A contact-polarized dermoscopy image of a skin lesion. The chart records no first-degree relative with melanoma and no prior melanoma. A female subject about 20 years old — 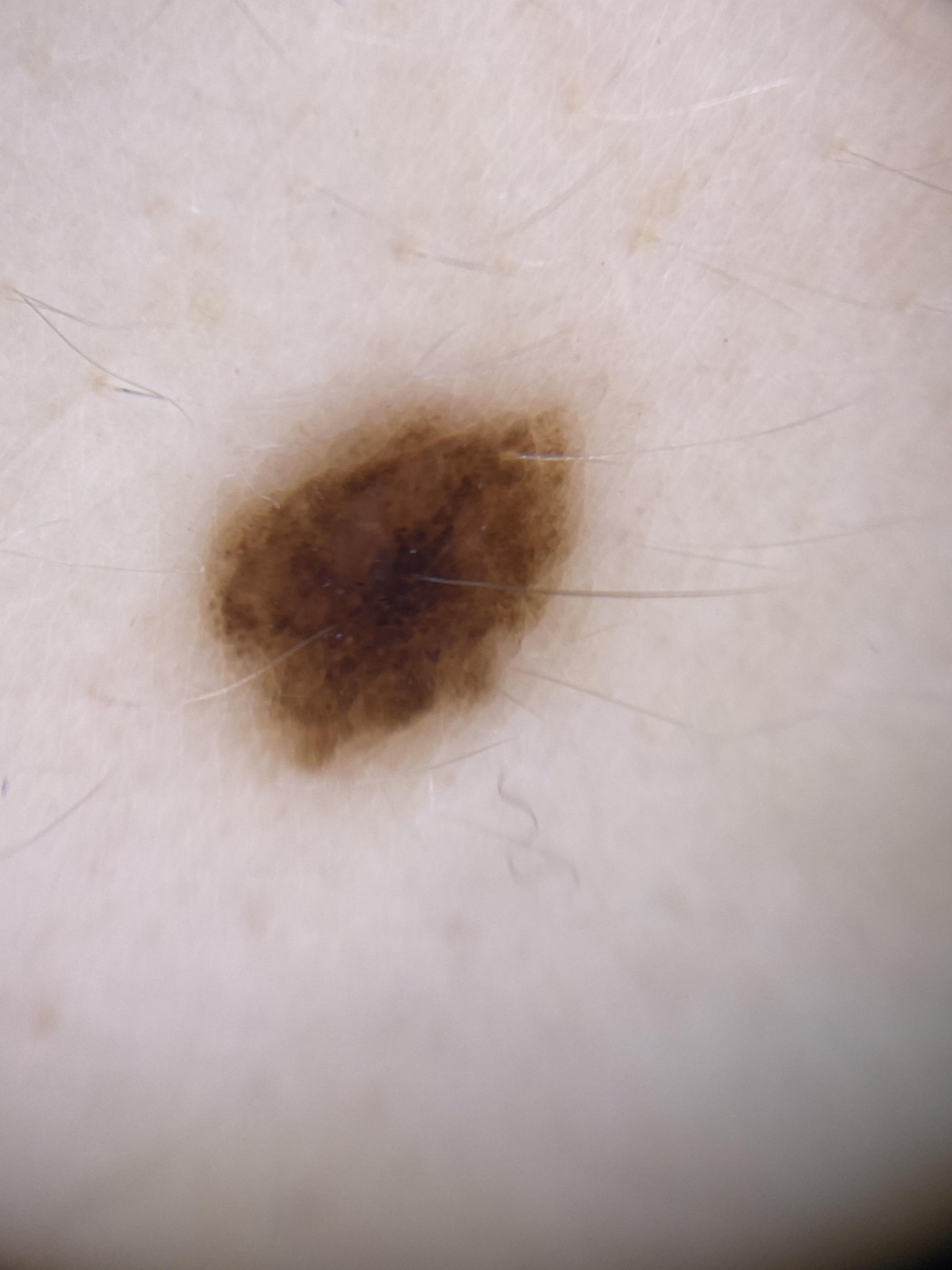<record>
<lesion_location>
<region>the trunk</region>
<detail>the anterior trunk</detail>
</lesion_location>
<diagnosis>
<name>Nevus</name>
<malignancy>benign</malignancy>
<confirmation>expert clinical impression</confirmation>
<lineage>melanocytic</lineage>
</diagnosis>
</record>